The lesion involves the leg. Female subject, age 30–39. The patient described the issue as a pigmentary problem. The patient reported no relevant symptoms from the lesion. The photograph was taken at a distance. Skin tone: Fitzpatrick skin type IV; lay graders estimated MST 1 or 3 (two reviewer pools disagreed). The patient reported no systemic symptoms. Texture is reported as flat: 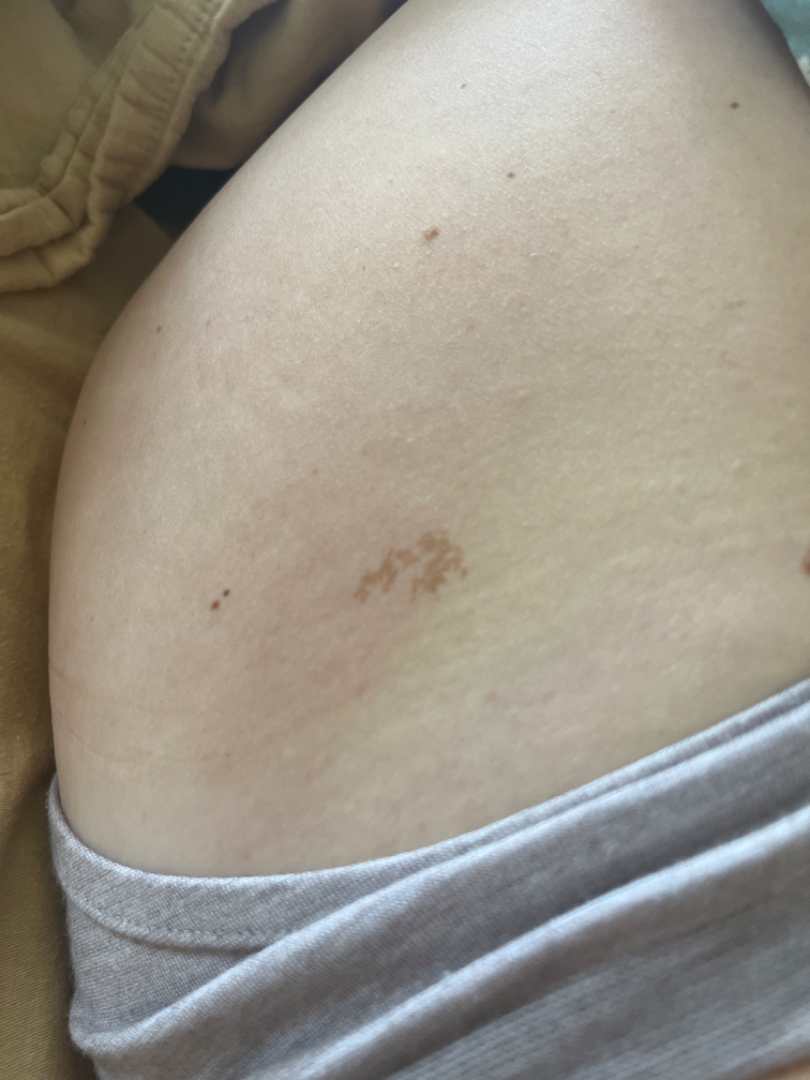{
  "assessment": "ungradable on photographic review"
}